A dermatoscopic image of a skin lesion.
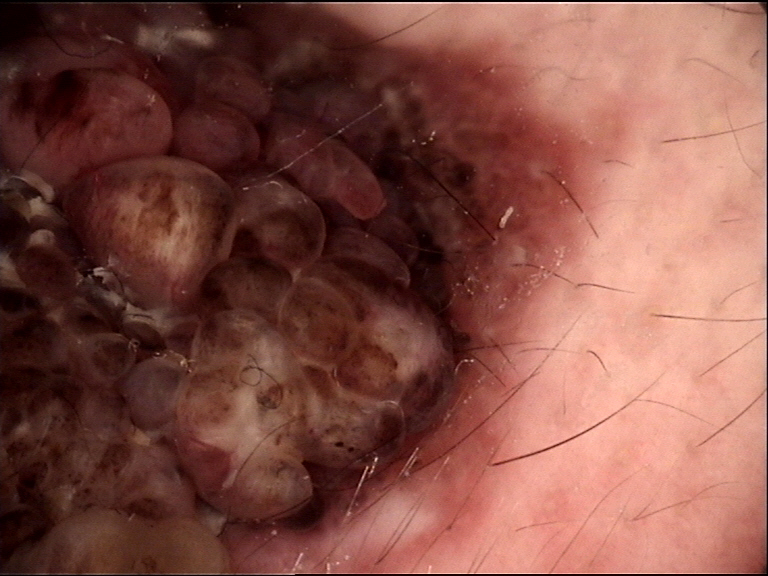Diagnosed as a banal lesion — a congenital compound nevus.